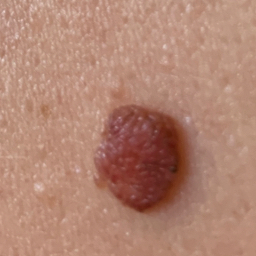Findings: A subject in their early 30s. A clinical photo of a skin lesion taken with a smartphone. The lesion is on the back. Per patient report, the lesion is elevated, but does not hurt and has not grown. Impression: Diagnosed by dermatologist consensus as a nevus.